A dermoscopic close-up of a skin lesion: 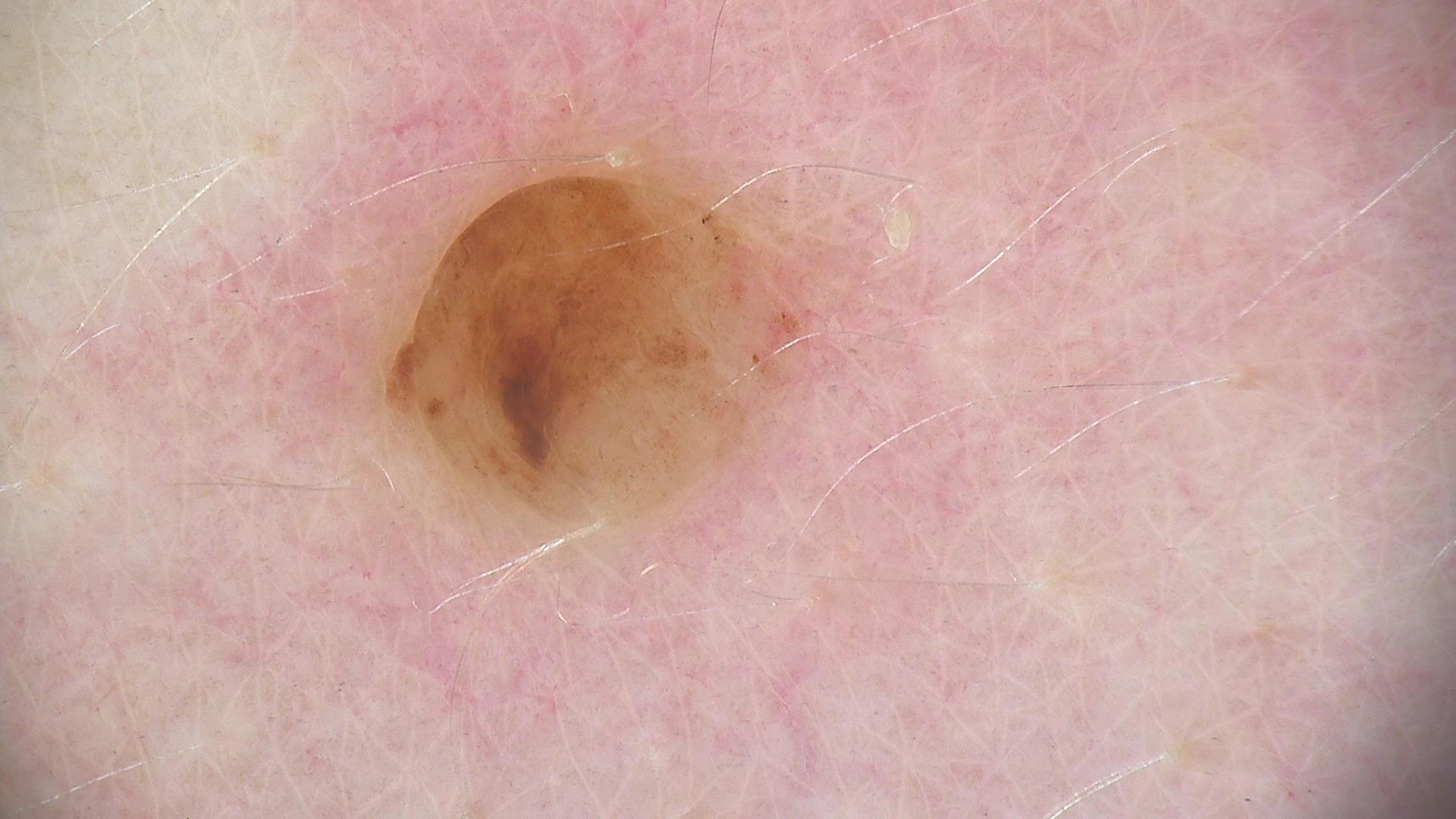Case:
The architecture is that of a banal lesion.
Impression:
Classified as a dermal nevus.